A dermoscopic image of a skin lesion.
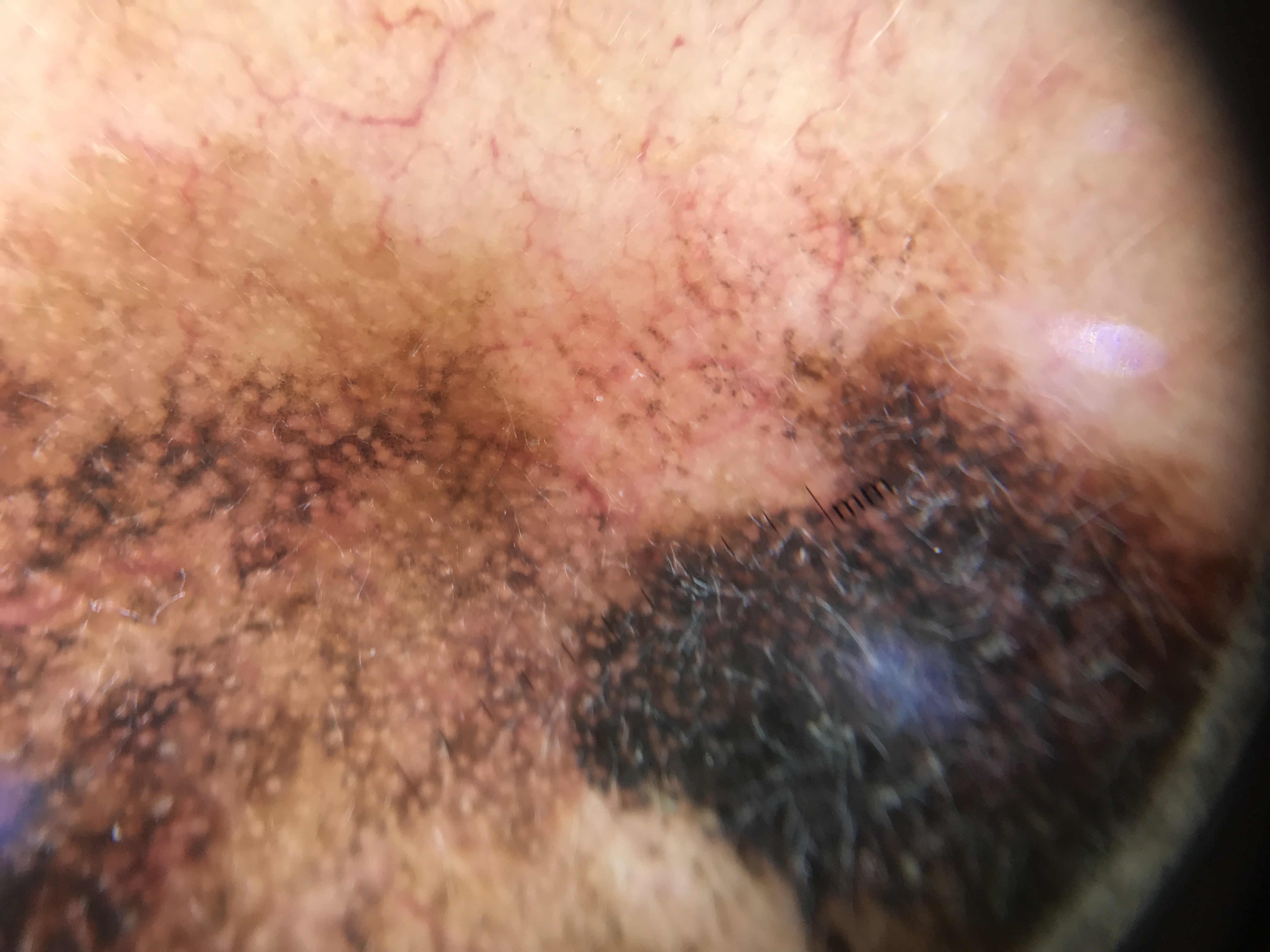Diagnosis:
Histopathologically confirmed as a skin cancer — a lentigo maligna.